A female subject 60 years of age; a dermoscopy image of a skin lesion; the patient reports a personal history of cancer and a personal history of skin cancer; the referring clinician suspected basal cell carcinoma; the patient describes having few moles overall; the patient says their skin tans without first burning:
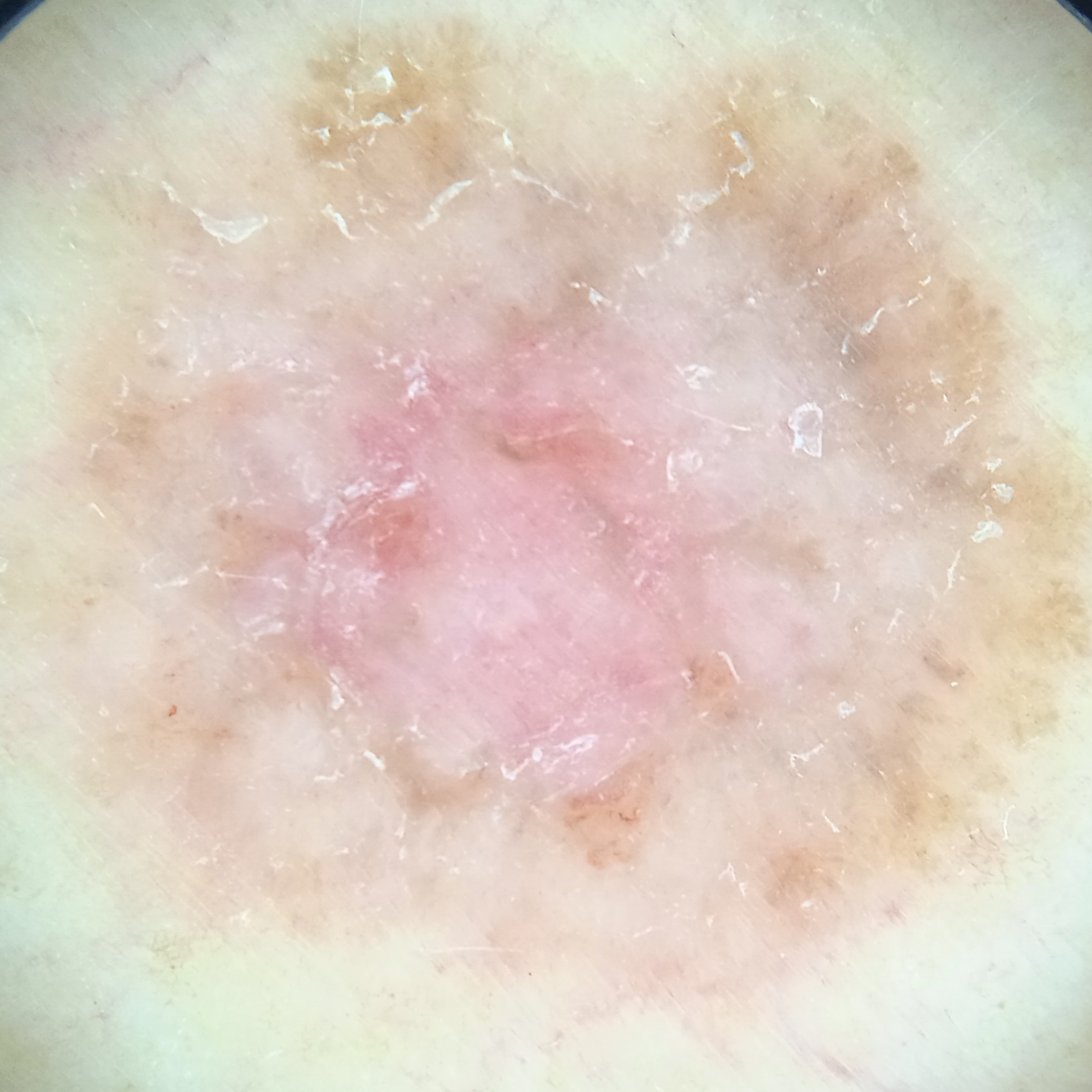Q: What is the anatomic site?
A: the torso
Q: What was the diagnosis?
A: basal cell carcinoma (dermatologist consensus)